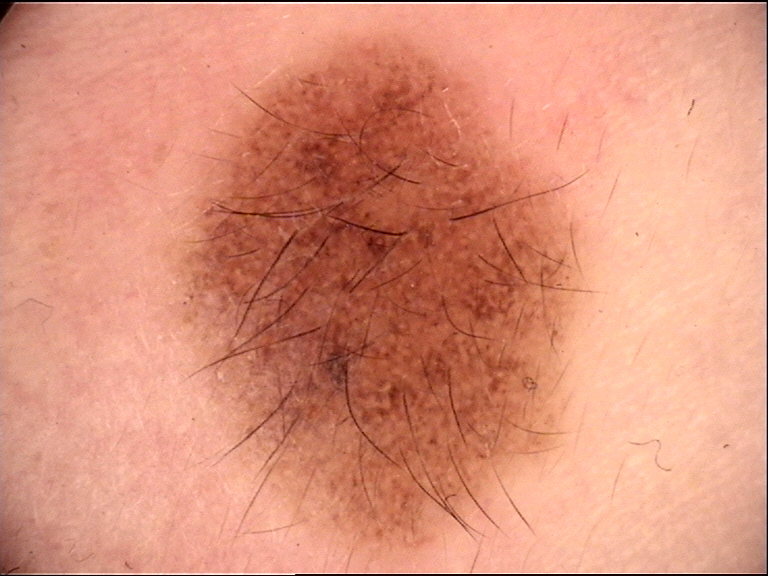Labeled as a banal lesion — a congenital compound nevus.